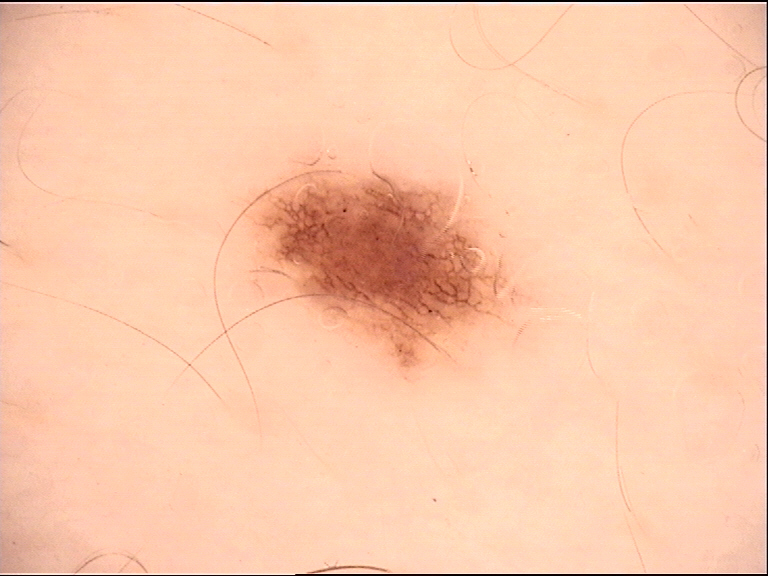Dermoscopy of a skin lesion.
Consistent with a benign lesion — a dysplastic junctional nevus.